The affected area is the leg; the photo was captured at a distance — 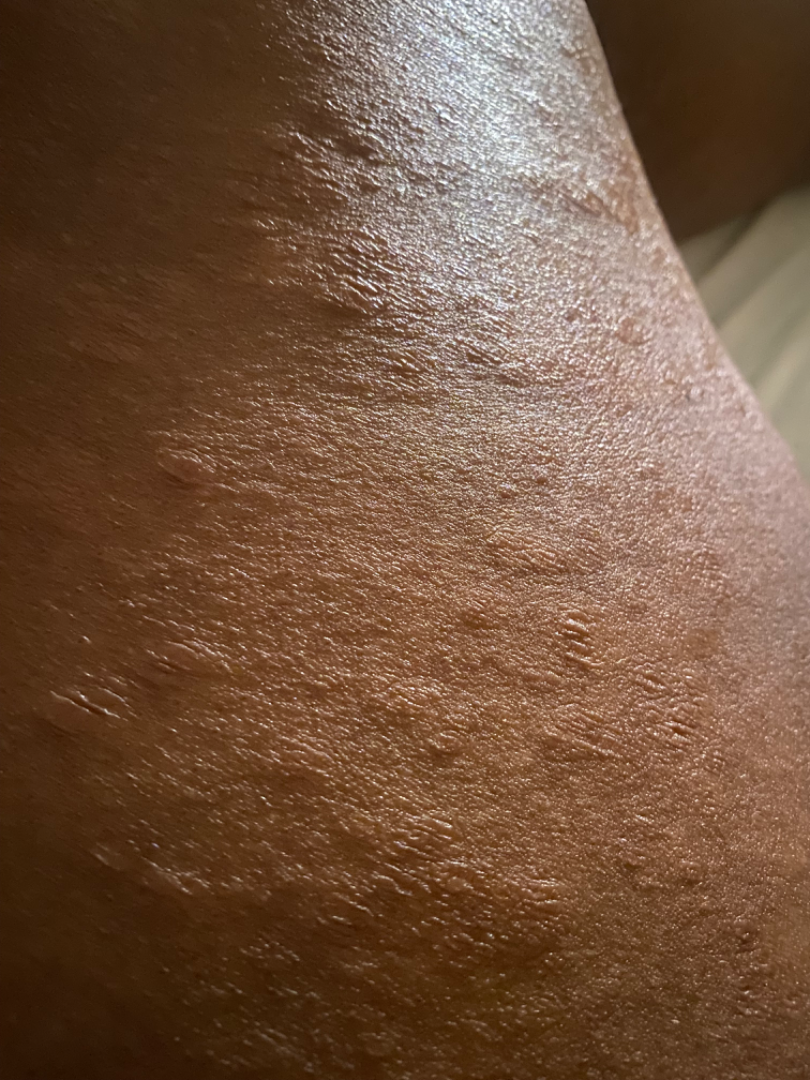| key | value |
|---|---|
| clinical impression | Cutaneous T Cell Lymphoma, Psoriasis and Eczema were each considered, in no particular order |